Located on the front of the torso and arm · an image taken at a distance.
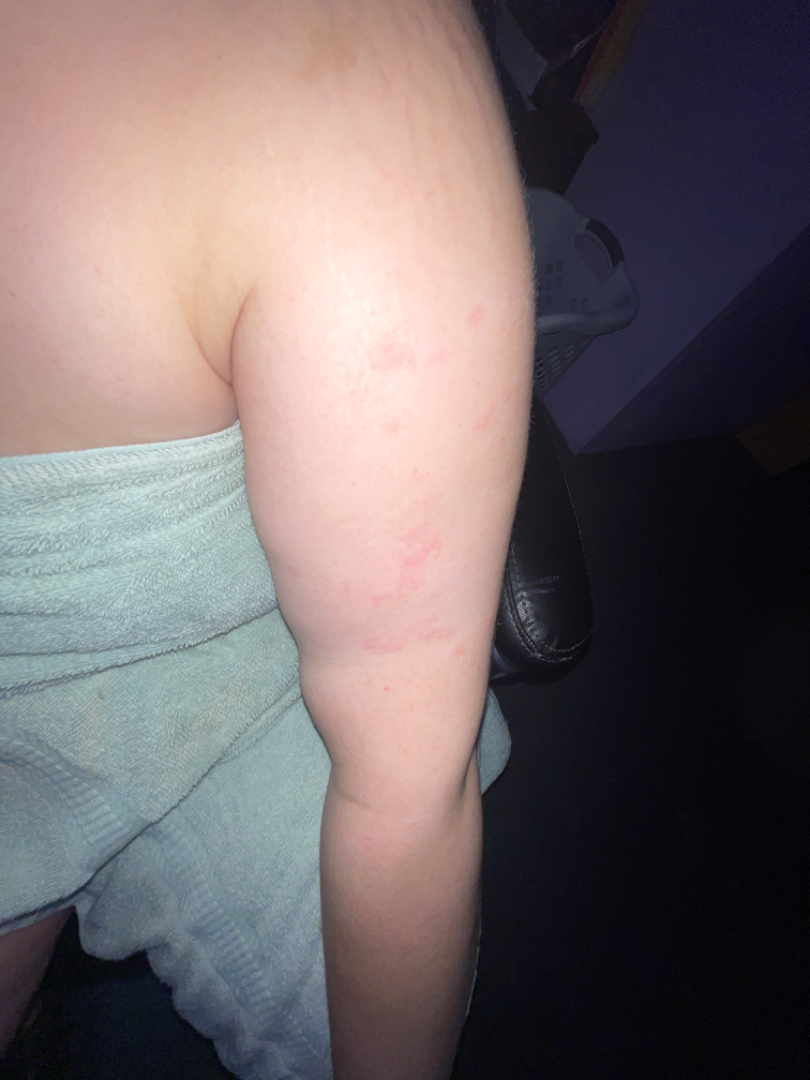clinical impression: most likely Allergic Contact Dermatitis; possibly Urticaria.